Dermoscopy of a skin lesion:
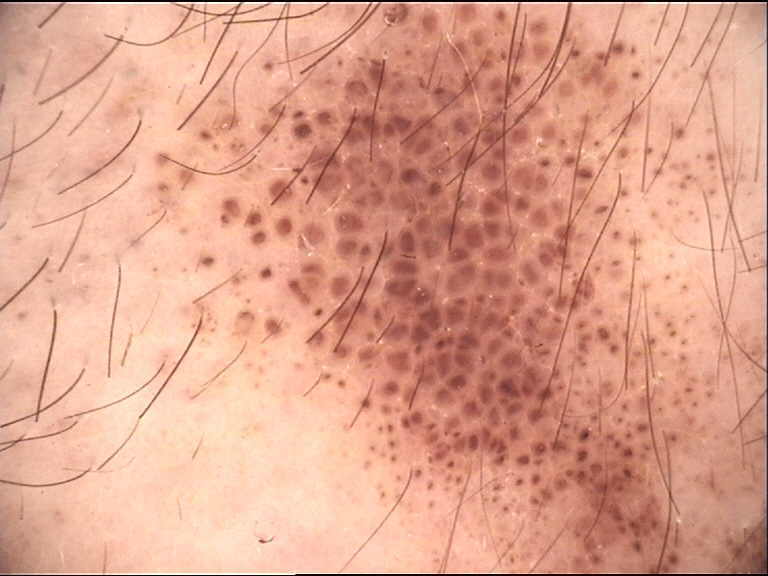Diagnosed as a banal lesion — a congenital compound nevus.